Dermoscopy of a skin lesion. A male subject aged around 65:
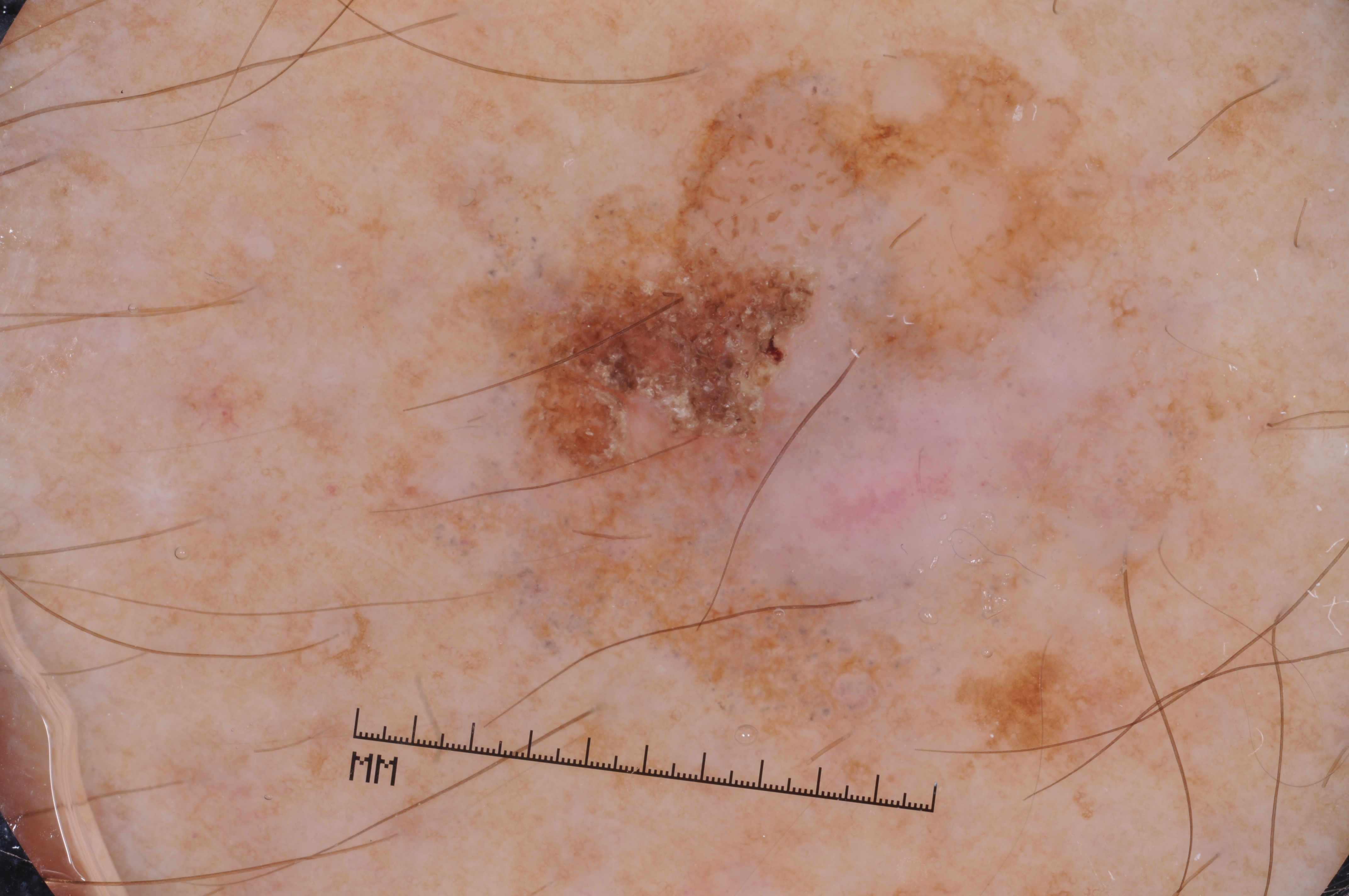Findings:
- dermoscopic features not present: milia-like cysts, negative network, pigment network, and streaks
- size: large
- bounding box: <bbox>430, 4, 1260, 835</bbox>
- diagnostic label: a seborrheic keratosis, a benign lesion